A dermoscopic view of a skin lesion — 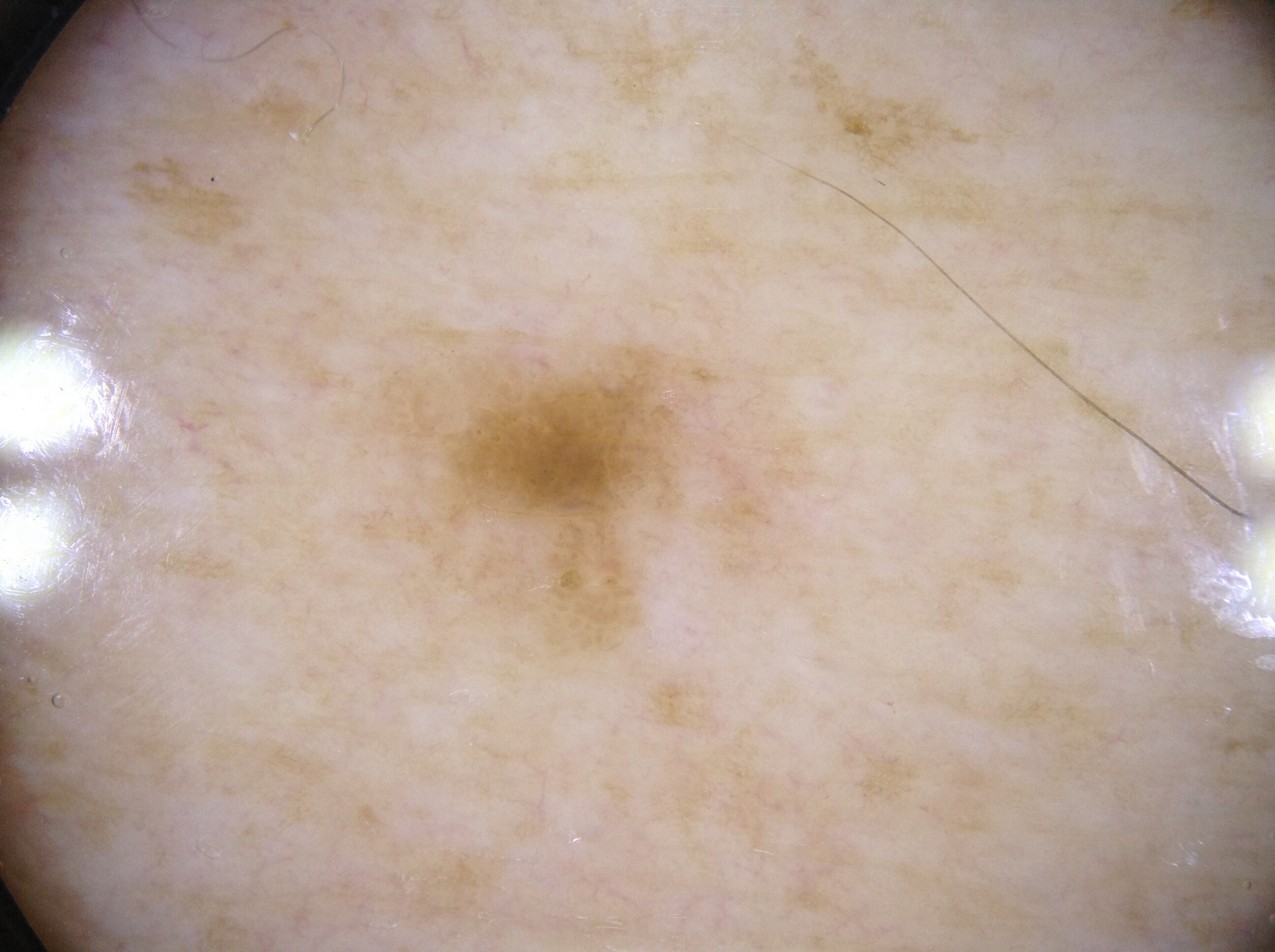As (left, top, right, bottom), the visible lesion spans bbox(329, 313, 853, 696). The diagnostic assessment was a seborrheic keratosis.